The condition has been present for about one day. Associated systemic symptoms include mouth sores and fever. The affected area is the back of the hand and palm. The patient notes the lesion is raised or bumpy. The photograph is a close-up of the affected area. The patient described the issue as a rash. Reported lesion symptoms include burning, bothersome appearance and pain. Female contributor, age 18–29. Skin tone: human graders estimated MST 3 (US pool) or 4 (India pool): 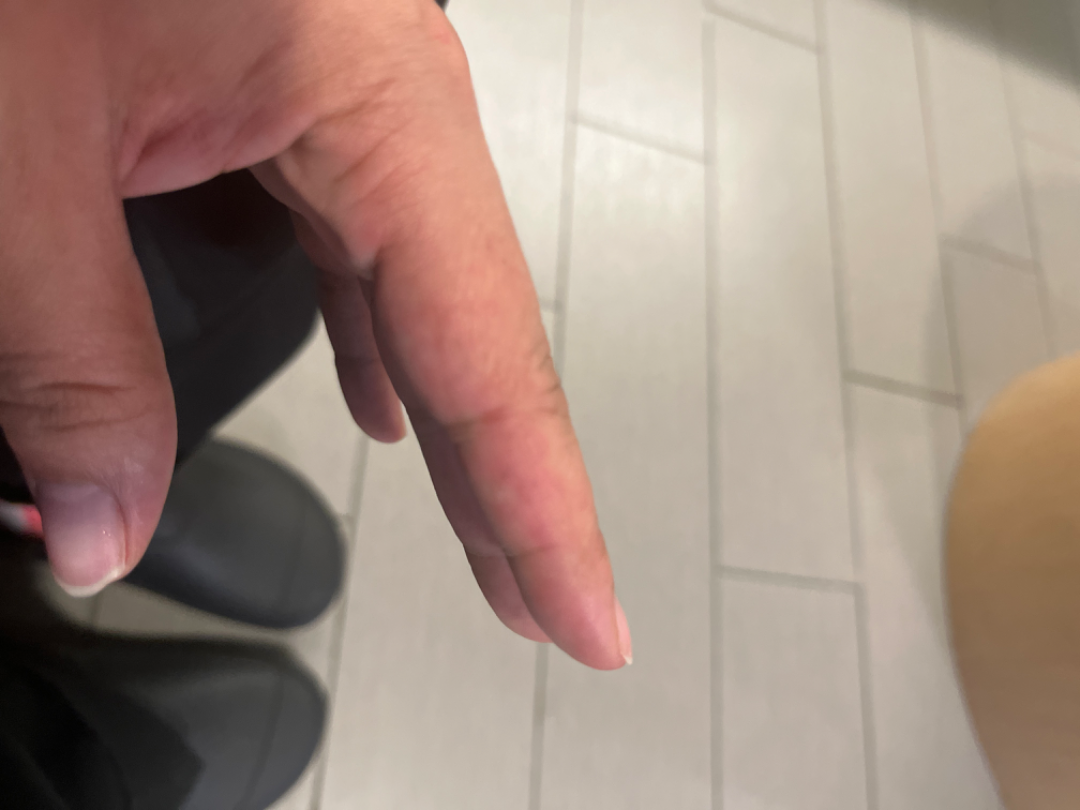dermatologist impression = Eczema (weight 0.67); Chilblain (weight 0.33).